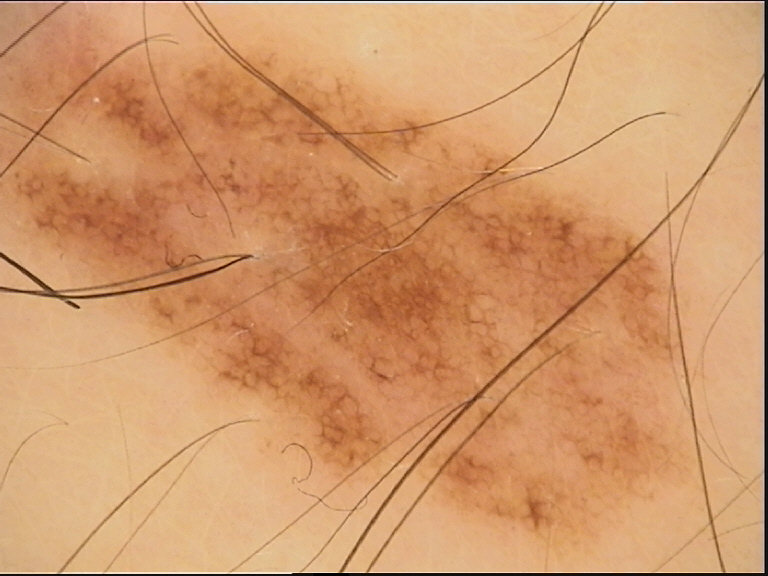class=dysplastic junctional nevus (expert consensus).